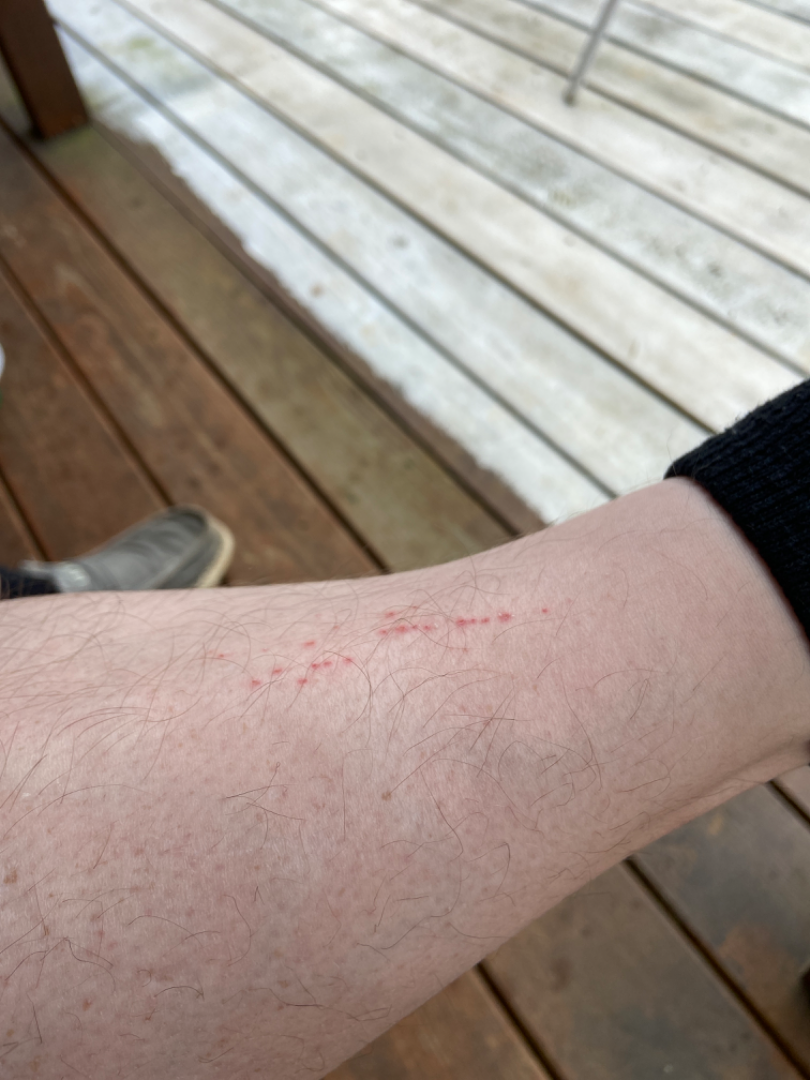Assessment:
The skin condition could not be confidently assessed from this image.
Clinical context:
The patient notes the lesion is flat. Reported duration is about one day. The lesion is associated with itching. The patient reported no systemic symptoms. Male contributor, age 18–29. The photograph was taken at an angle. The lesion involves the leg.